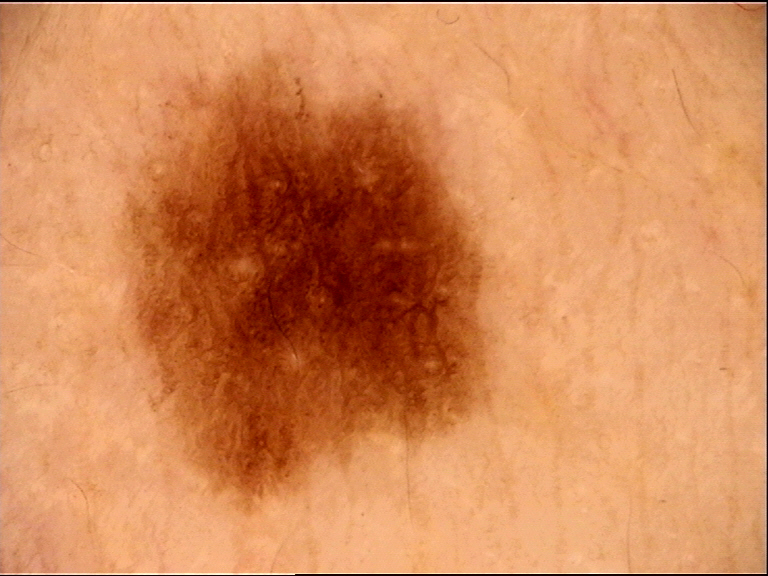Q: What is this lesion?
A: dysplastic junctional nevus (expert consensus)